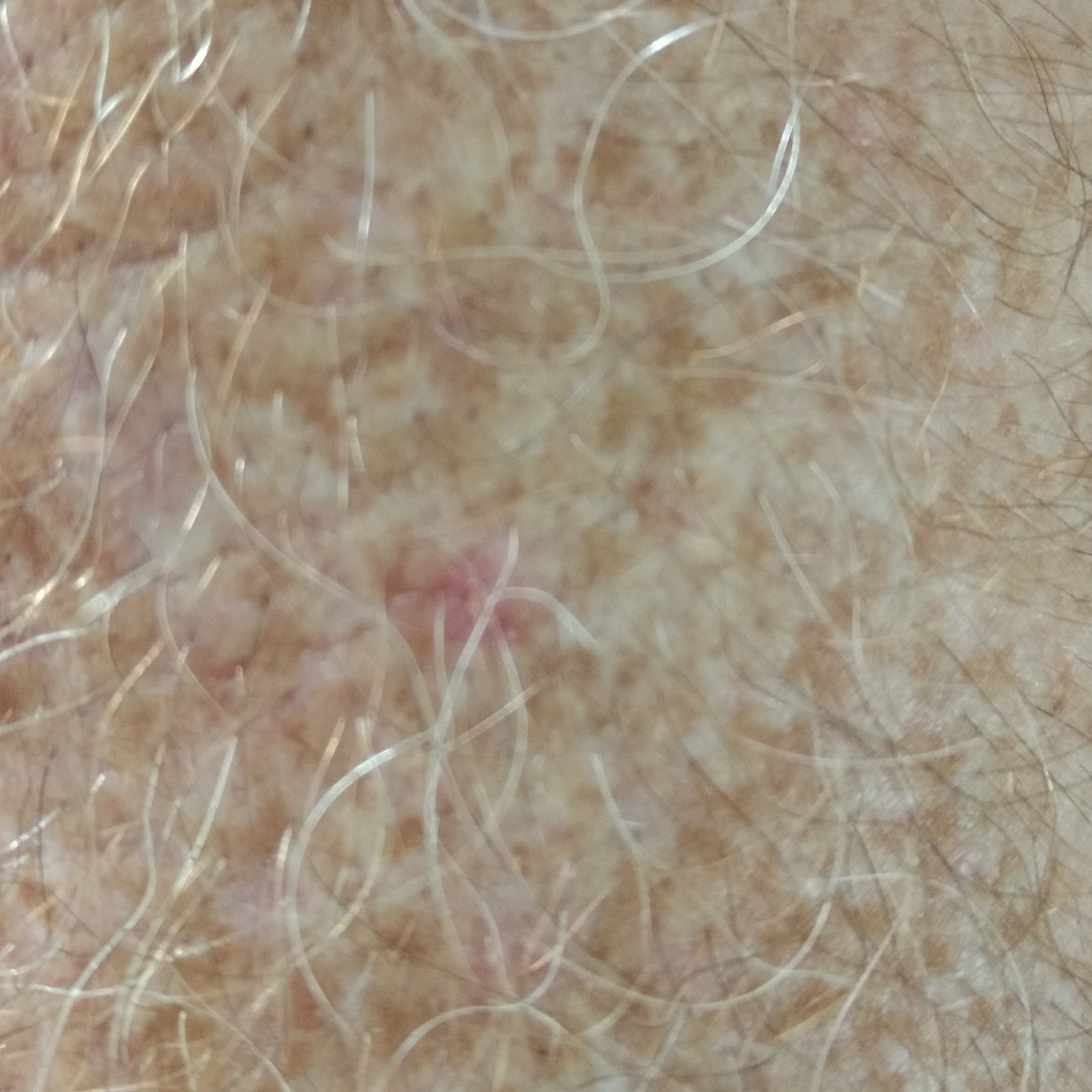A patient 54 years old. A smartphone photograph of a skin lesion. The lesion is located on a forearm. Consistent with an actinic keratosis.